Dermoscopy of a skin lesion.
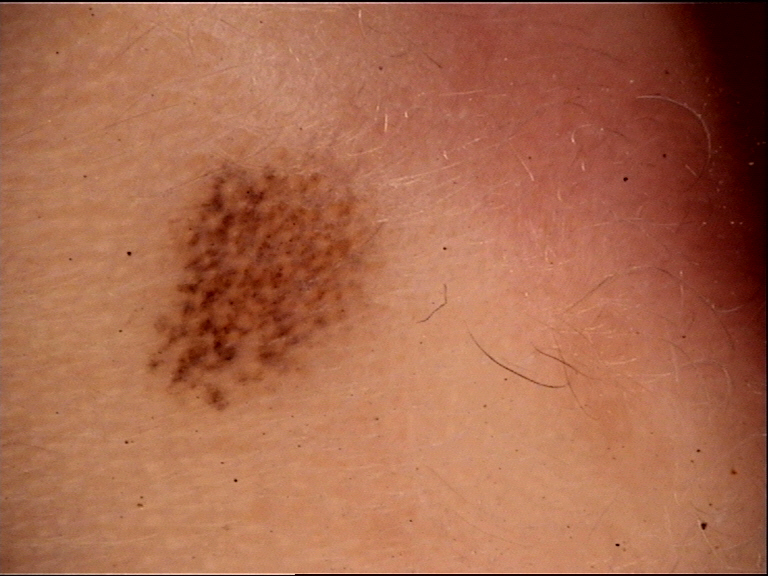class: Miescher nevus (expert consensus)